A smartphone photograph of a skin lesion. Fitzpatrick phototype III — 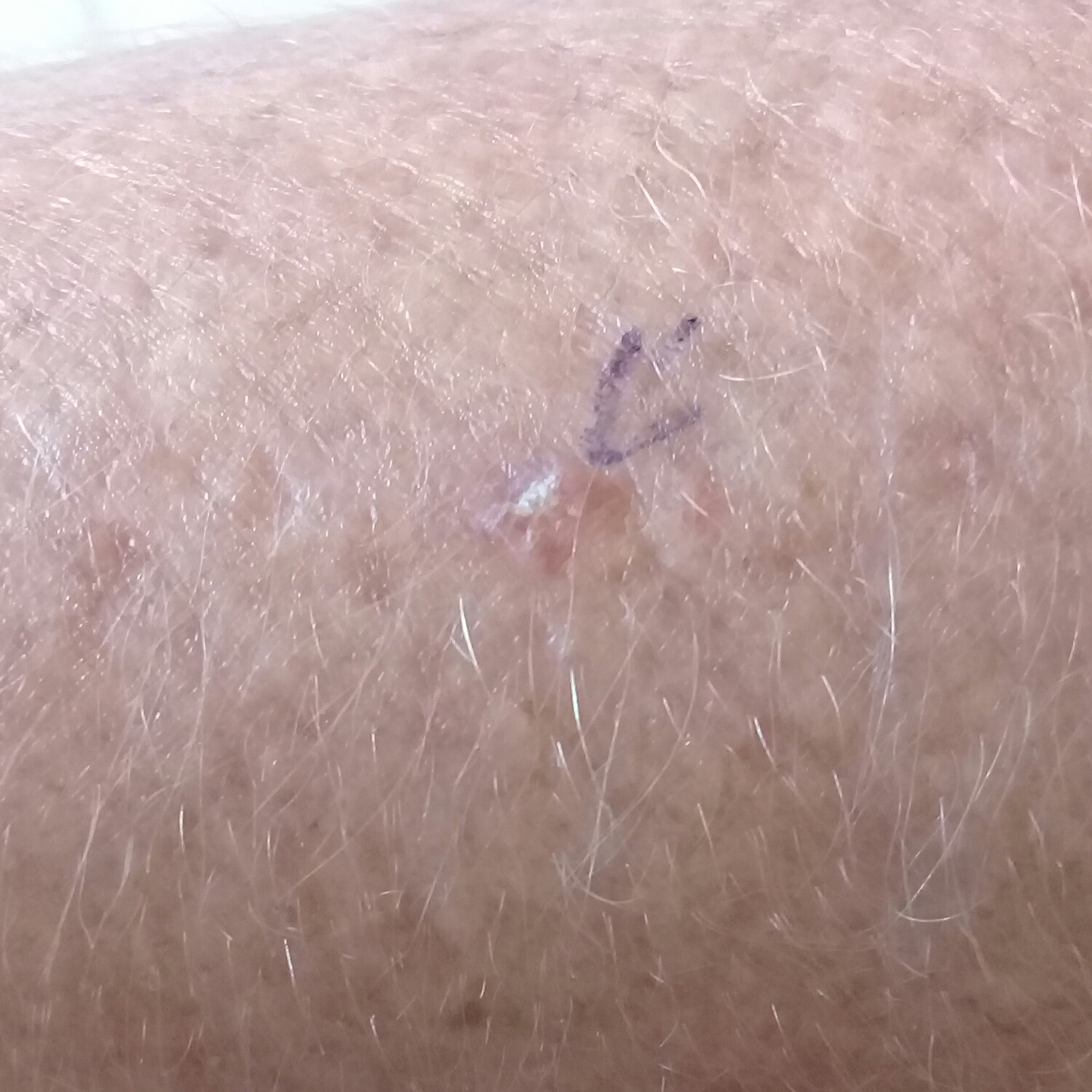Findings:
Located on a forearm. The lesion is roughly 10 by 10 mm. Asymptomatic by report.
Conclusion:
The clinical impression was an actinic keratosis.